A dermatoscopic image of a skin lesion: 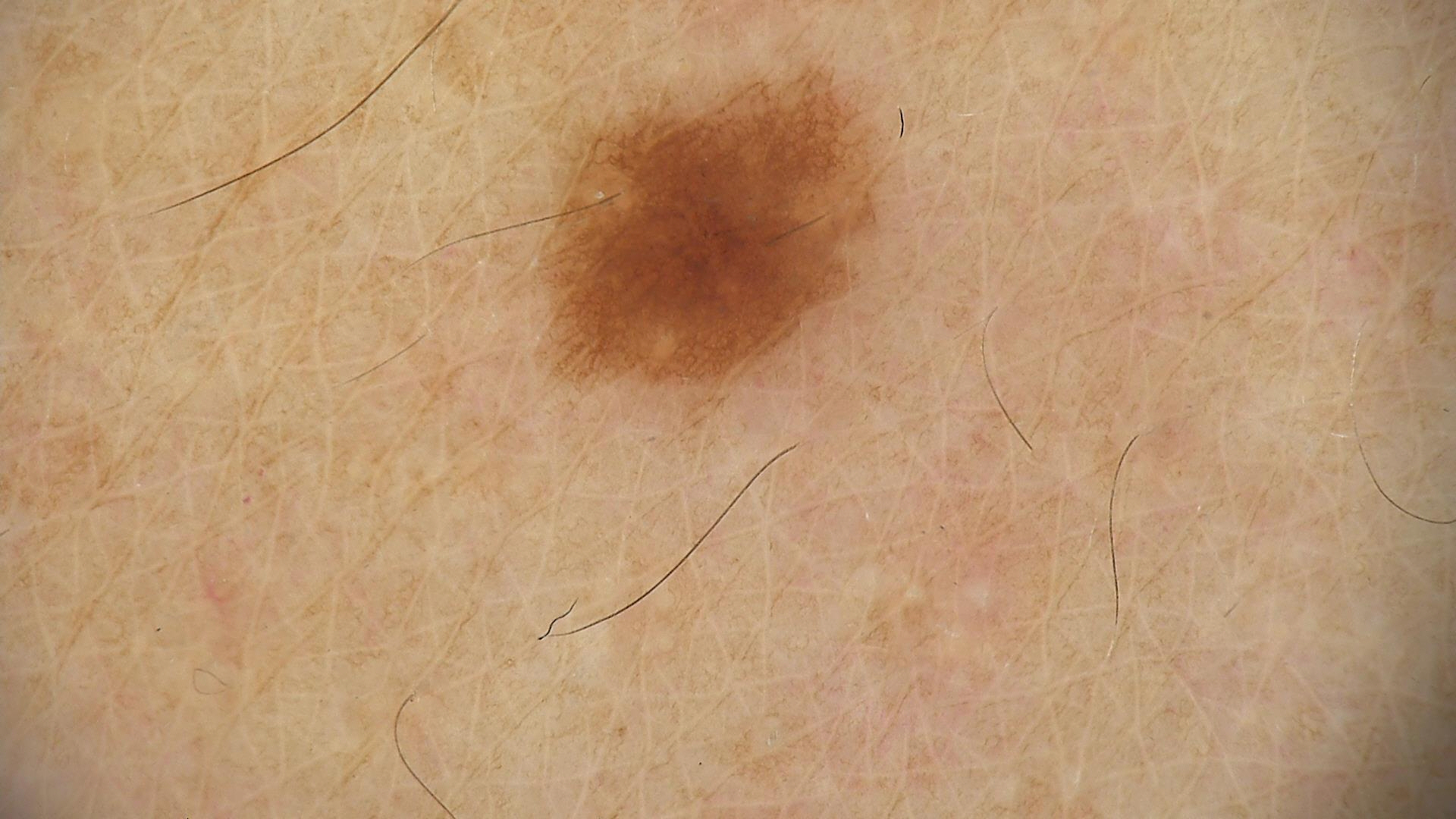| feature | finding |
|---|---|
| diagnosis | dysplastic junctional nevus (expert consensus) |